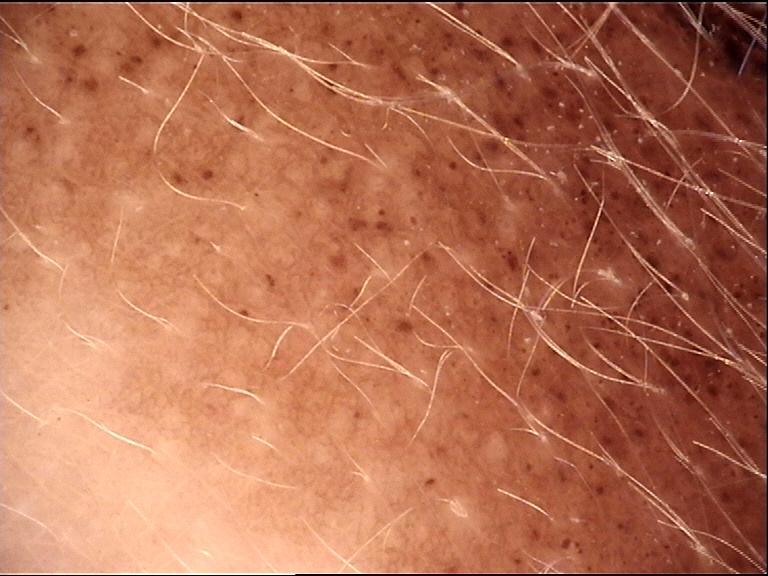The architecture is that of a banal lesion.
Labeled as a congenital junctional nevus.